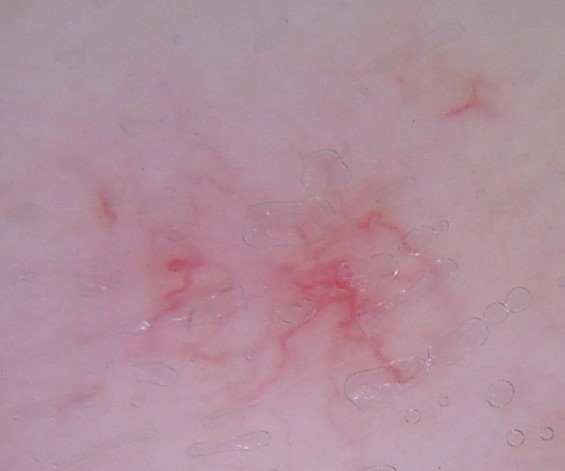Q: What is this lesion?
A: spider angioma (expert consensus)